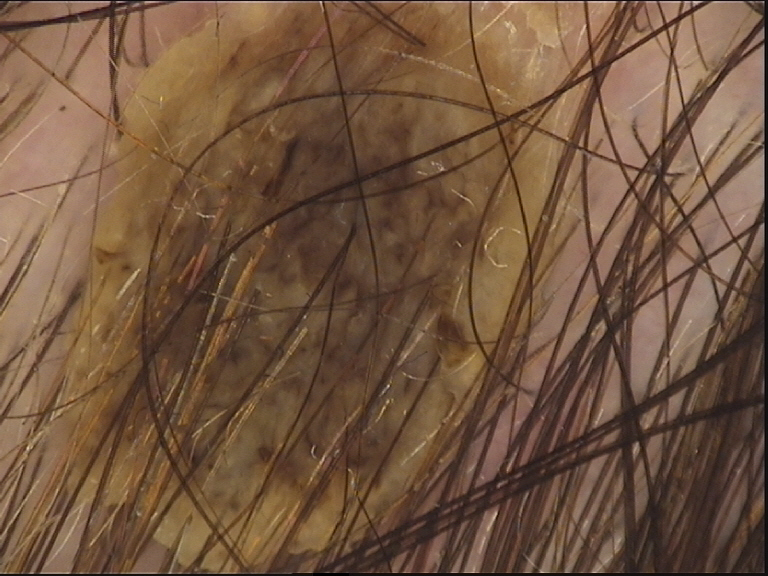<case>
  <diagnosis>
    <name>seborrheic keratosis</name>
    <code>sk</code>
    <malignancy>benign</malignancy>
    <super_class>non-melanocytic</super_class>
    <confirmation>expert consensus</confirmation>
  </diagnosis>
</case>